A dermoscopic photograph of a skin lesion.
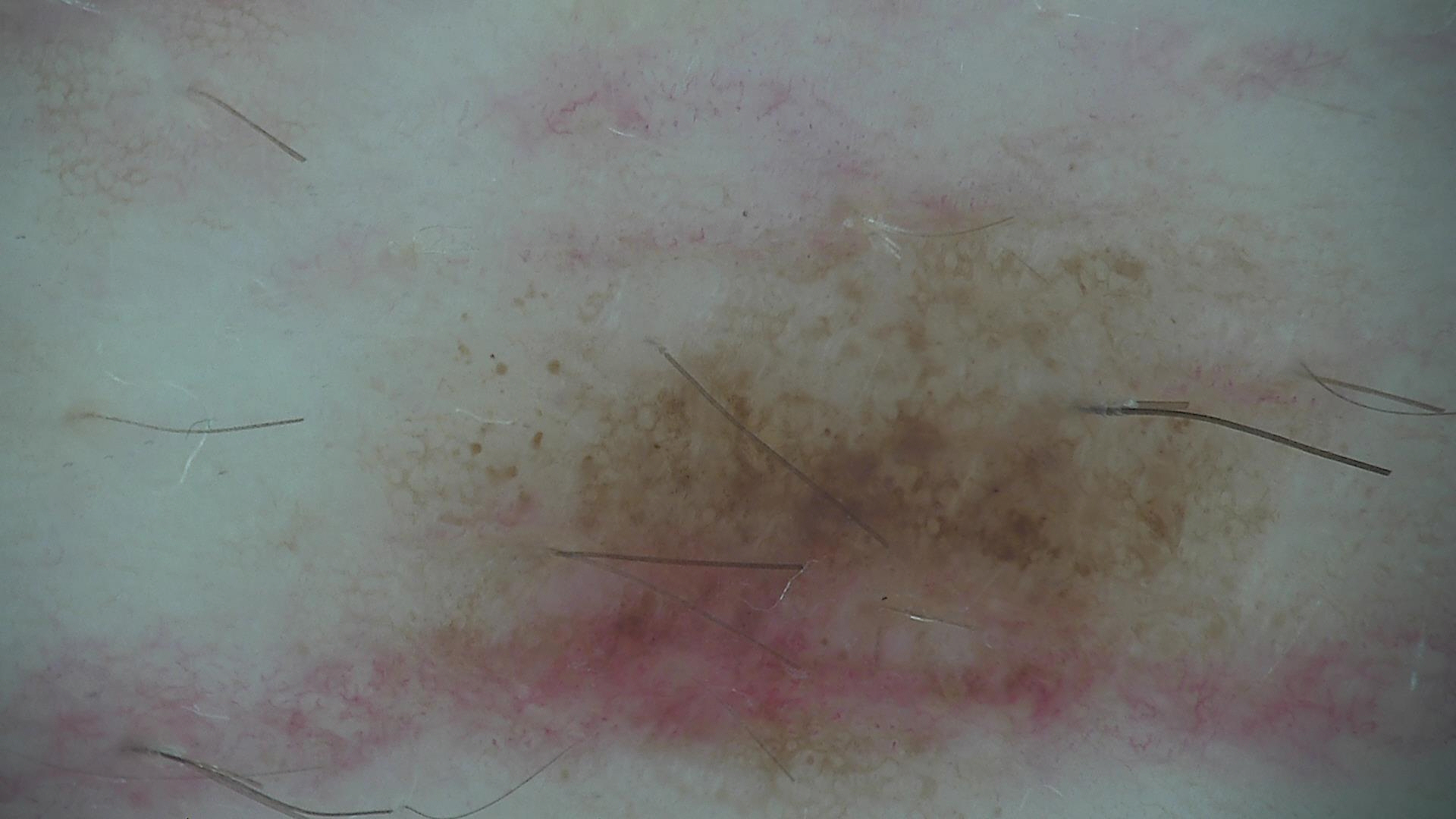{
  "diagnosis": {
    "name": "dysplastic junctional nevus",
    "code": "jd",
    "malignancy": "benign",
    "super_class": "melanocytic",
    "confirmation": "expert consensus"
  }
}